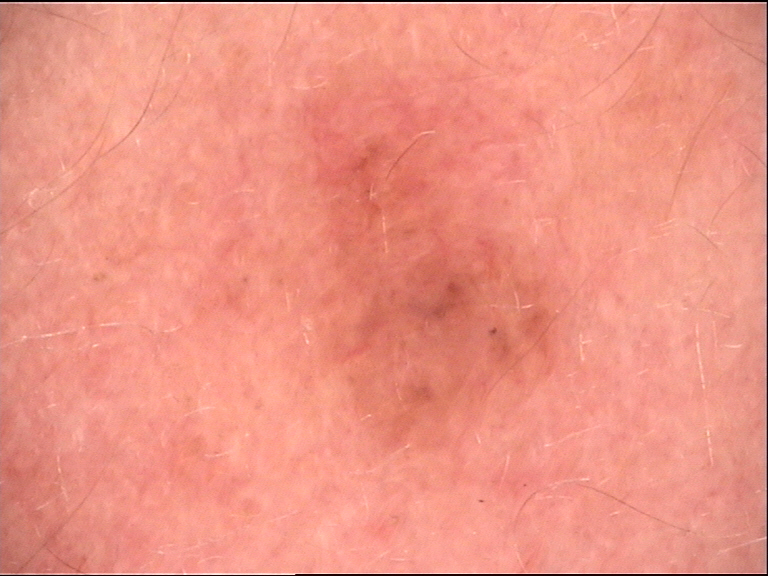Summary: Dermoscopy of a skin lesion. The morphology is that of a banal lesion. Impression: Diagnosed as a dermal nevus.